The photograph was taken at an angle.
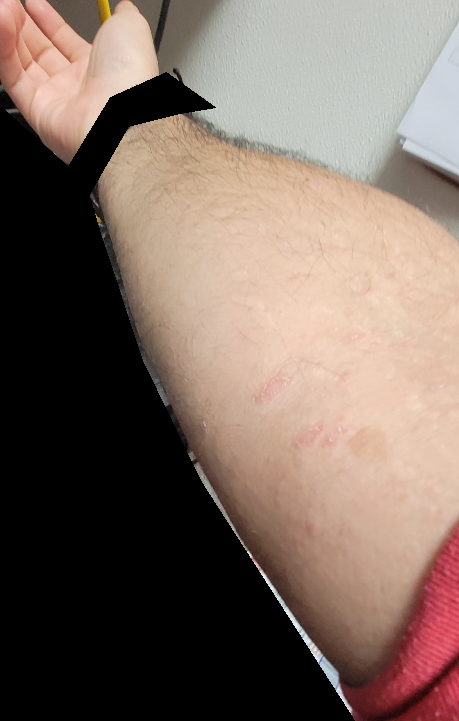The differential includes Tinea and Pityriasis rosea, with no clear leading consideration; less likely is Psoriasis.